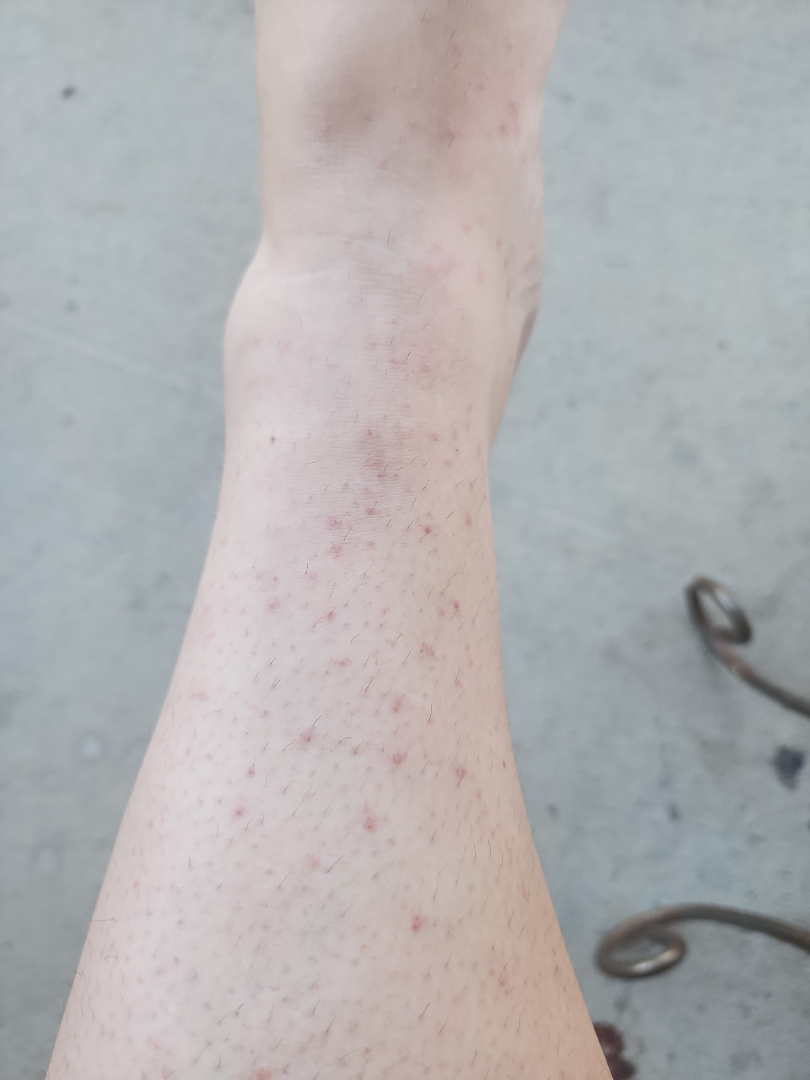The lesion involves the palm, arm, leg, back of the torso, head or neck, front of the torso and back of the hand. Symptoms reported: itching. This is a close-up image. Reviewed remotely by one dermatologist: consistent with Folliculitis.